A patient age 75 · a clinical close-up photograph of a skin lesion.
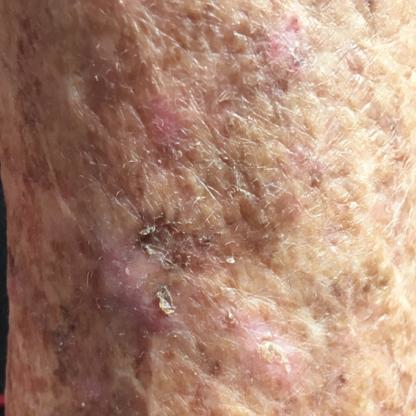reported symptoms — bleeding, itching
assessment — actinic keratosis (clinical consensus)